A dermoscopic image of a skin lesion.
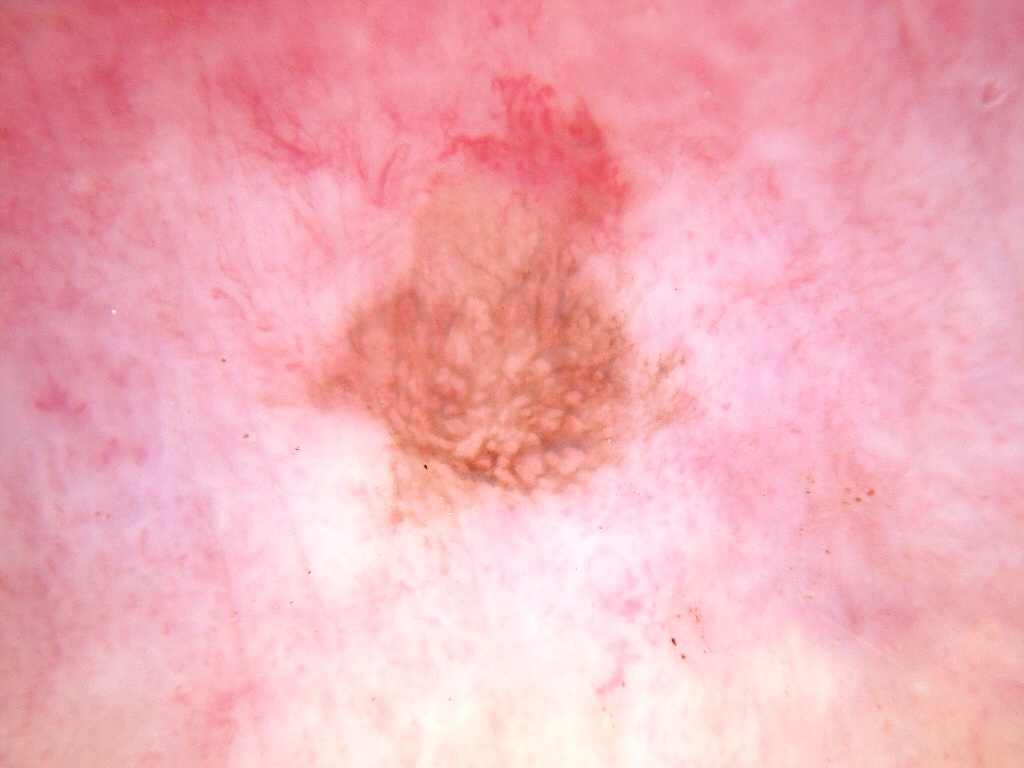<dermoscopy>
<lesion_extent>
  <approx_field_fraction_pct>12</approx_field_fraction_pct>
</lesion_extent>
<lesion_location>
  <bbox_xyxy>306, 168, 715, 534</bbox_xyxy>
</lesion_location>
<dermoscopic_features>
  <present/>
  <absent>streaks, globules</absent>
</dermoscopic_features>
<diagnosis>
  <malignancy>benign</malignancy>
  <provenance>clinical</provenance>
</diagnosis>
</dermoscopy>